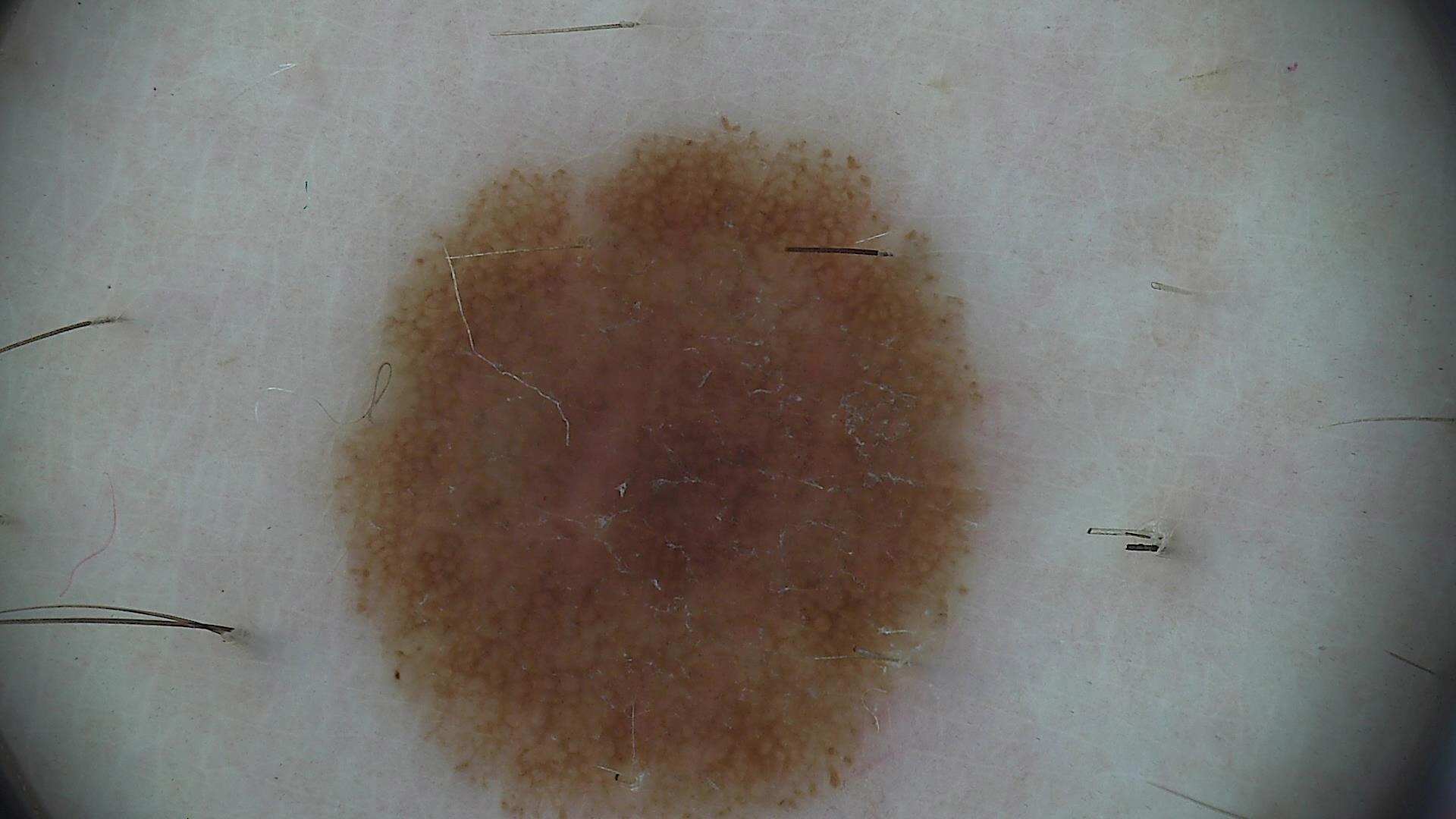diagnosis:
  name: dysplastic junctional nevus
  code: jd
  malignancy: benign
  super_class: melanocytic
  confirmation: expert consensus